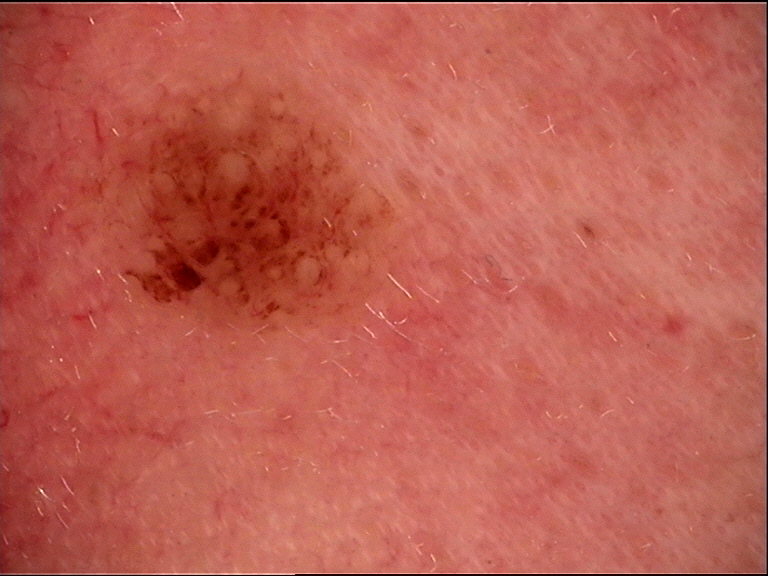Summary: A dermoscopic close-up of a skin lesion. The morphology is that of a banal lesion. Impression: Consistent with a compound nevus.